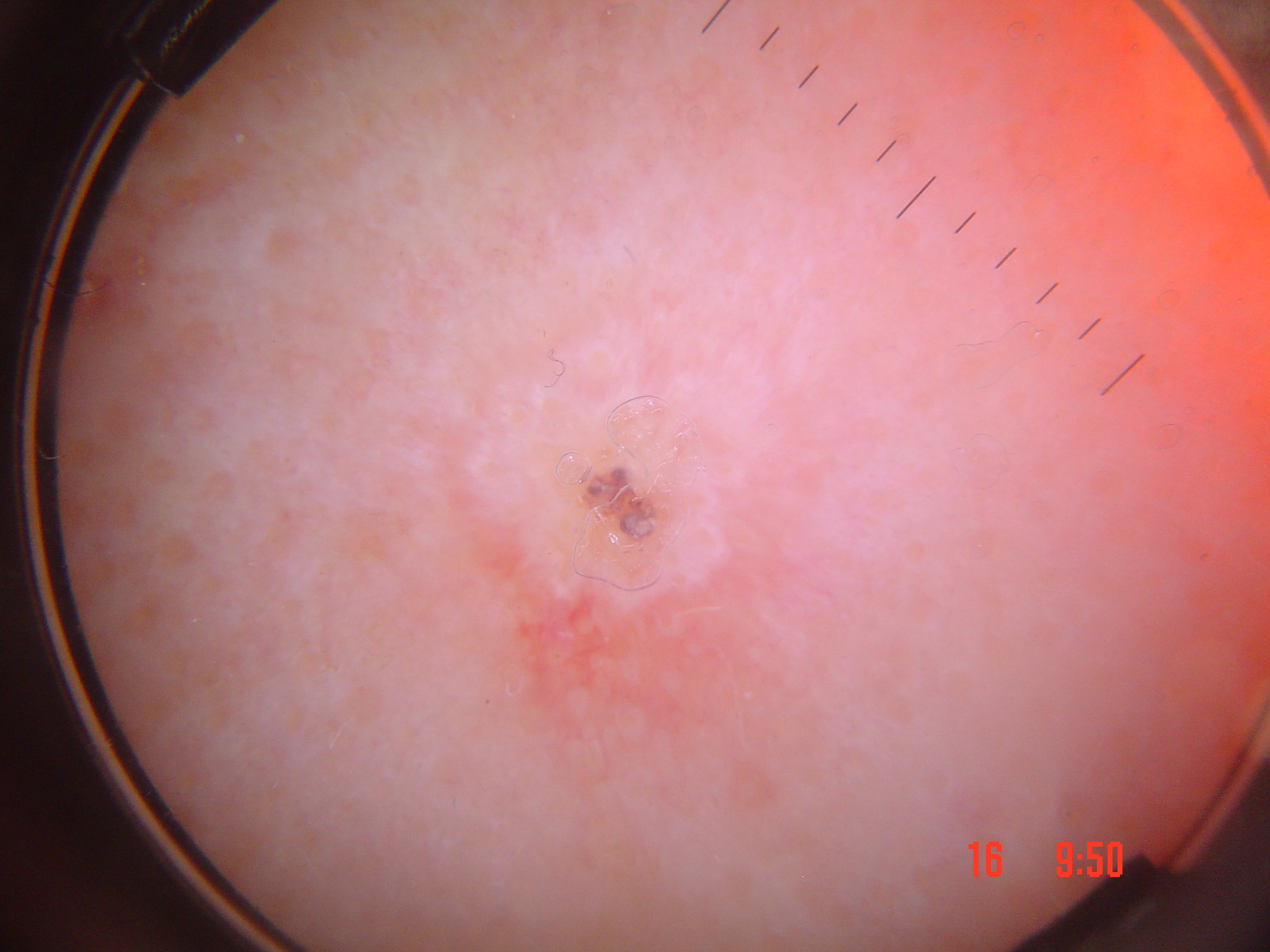{
  "image": "dermatoscopy",
  "lesion_type": {
    "main_class": "keratinocytic"
  },
  "diagnosis": {
    "name": "squamous cell carcinoma",
    "code": "scc",
    "malignancy": "malignant",
    "super_class": "non-melanocytic",
    "confirmation": "histopathology"
  }
}